A skin lesion imaged with a dermatoscope. A female patient roughly 50 years of age.
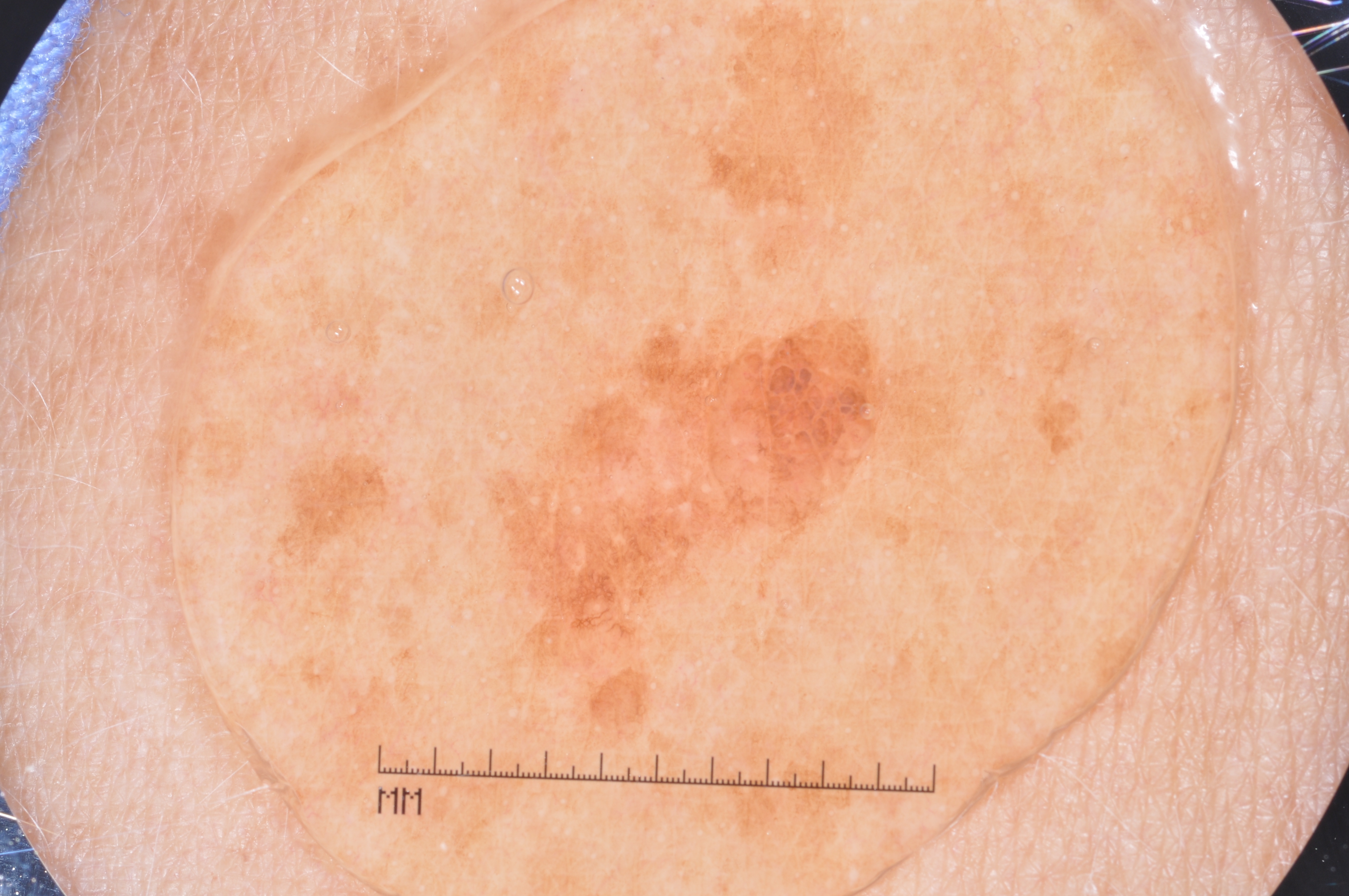In (x1, y1, x2, y2) order, the lesion occupies the region box(474, 291, 900, 767).
On dermoscopy, the lesion shows milia-like cysts and pigment network; no negative network or streaks.
Consistent with a melanocytic nevus, a benign lesion.